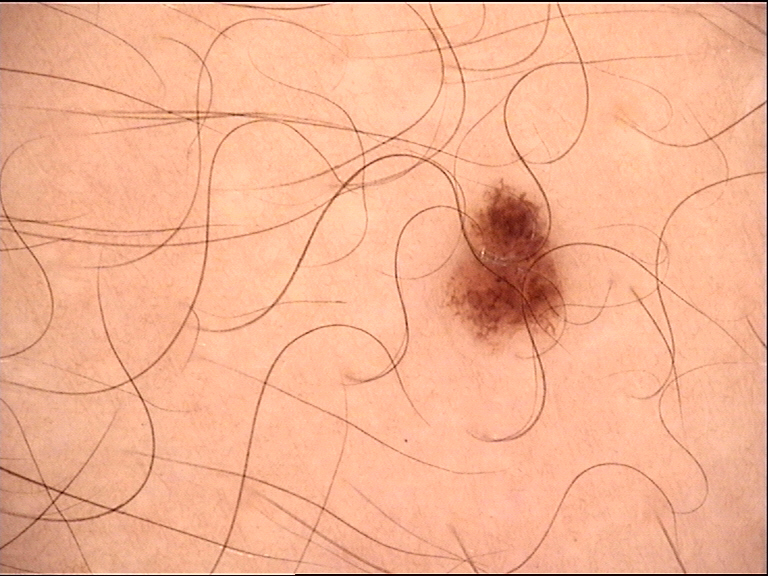| key | value |
|---|---|
| label | dysplastic junctional nevus (expert consensus) |